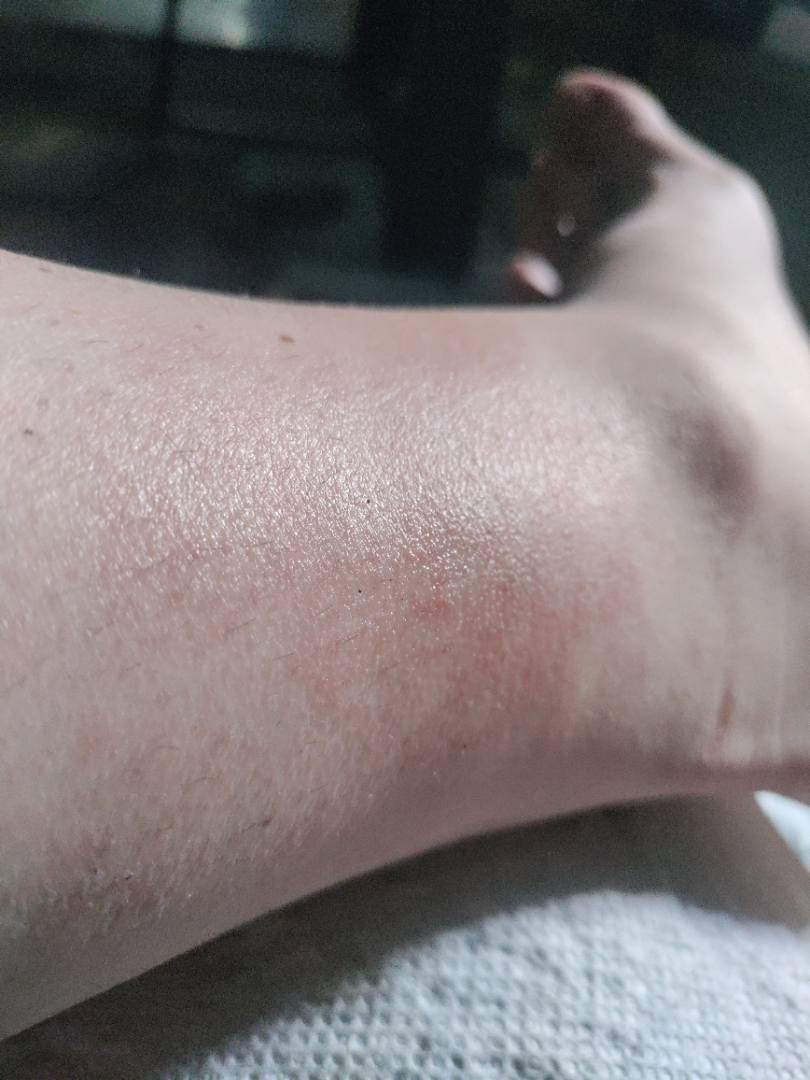The patient is 30–39, female. Located on the leg. The photograph was taken at an angle. No relevant lesion symptoms reported. The patient considered this a rash. The lesion is described as flat. Present for about one day. On remote dermatologist review, the differential includes Stasis Dermatitis; Acute dermatitis, NOS; and Allergic Contact Dermatitis, with no clear leading consideration.